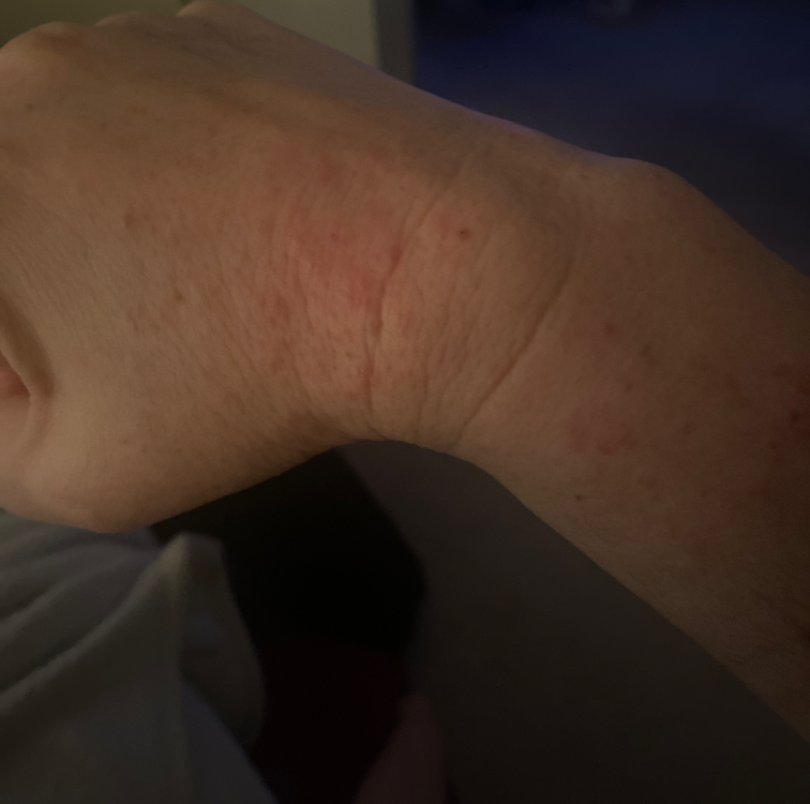Case summary:
– assessment · ungradable on photographic review
– shot type · at a distance